Located on the leg, a close-up photograph:
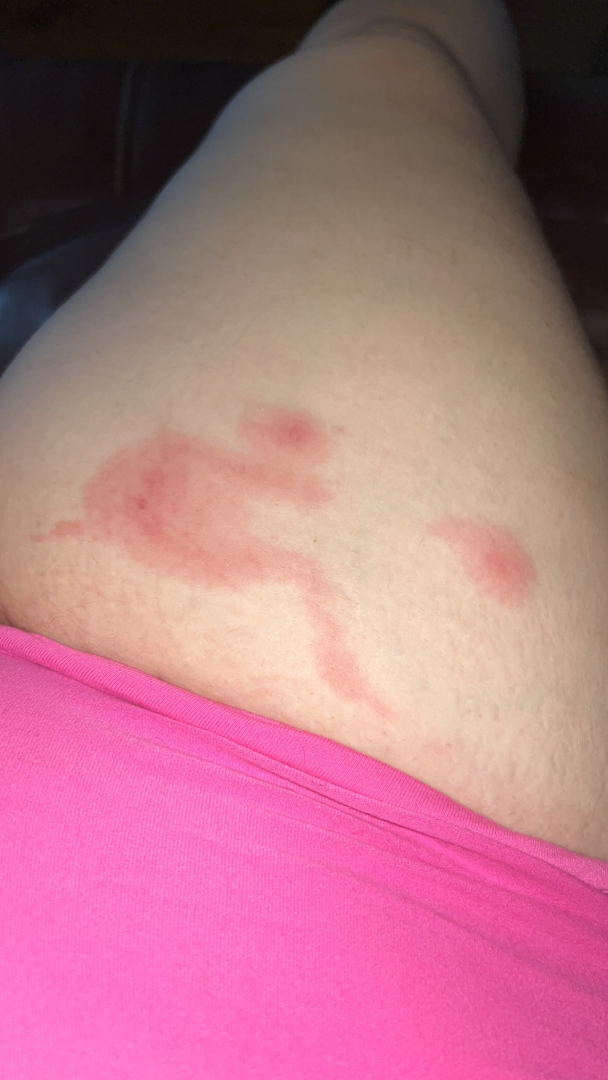assessment = ungradable on photographic review
skin tone = human graders estimated MST 2–3
symptoms = burning, pain, enlargement, itching and bothersome appearance
associated systemic symptoms = none reported
present for = less than one week
described texture = raised or bumpy